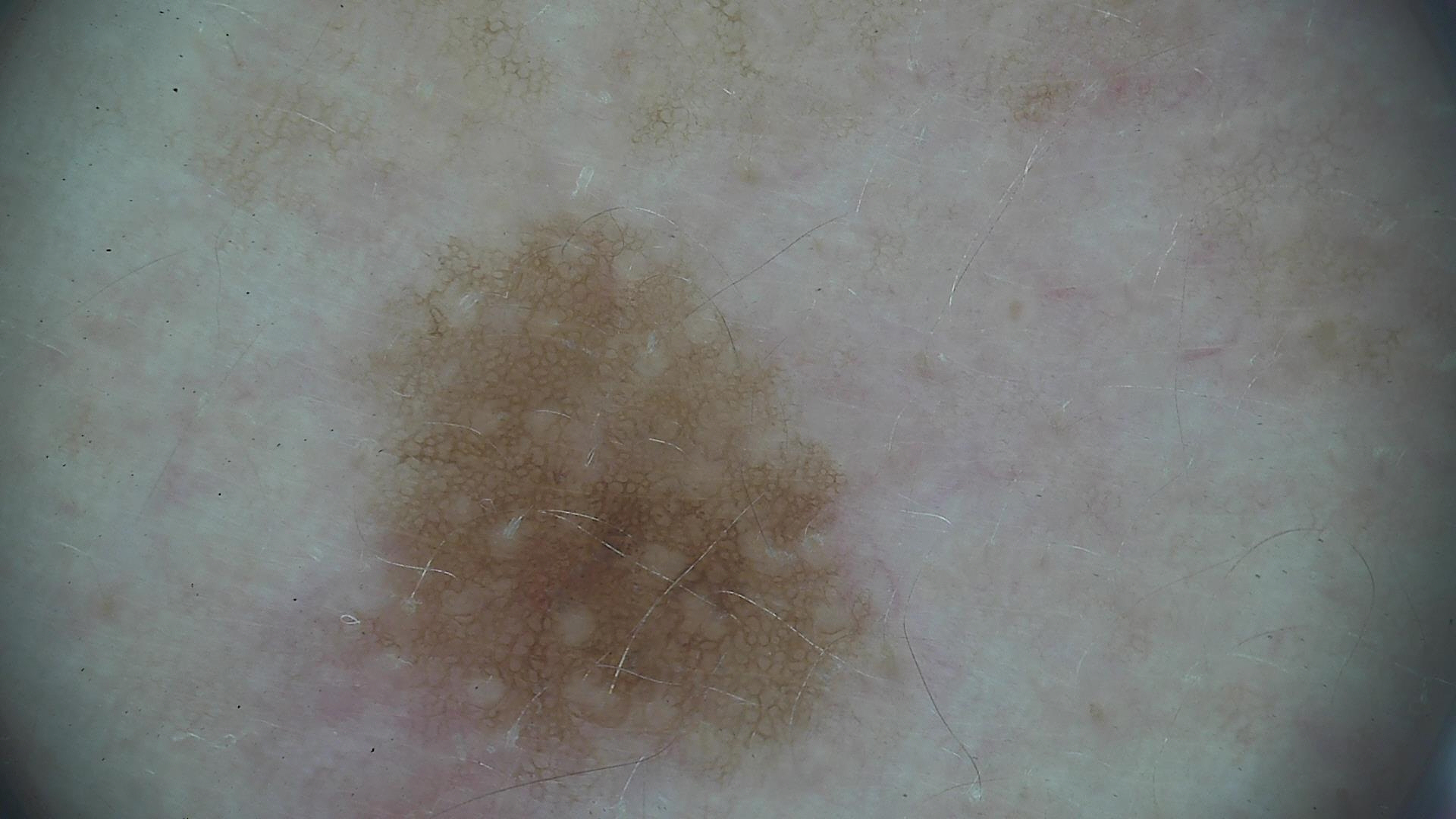- modality — dermoscopy
- diagnosis — dysplastic junctional nevus (expert consensus)